A dermoscopic photograph of a skin lesion.
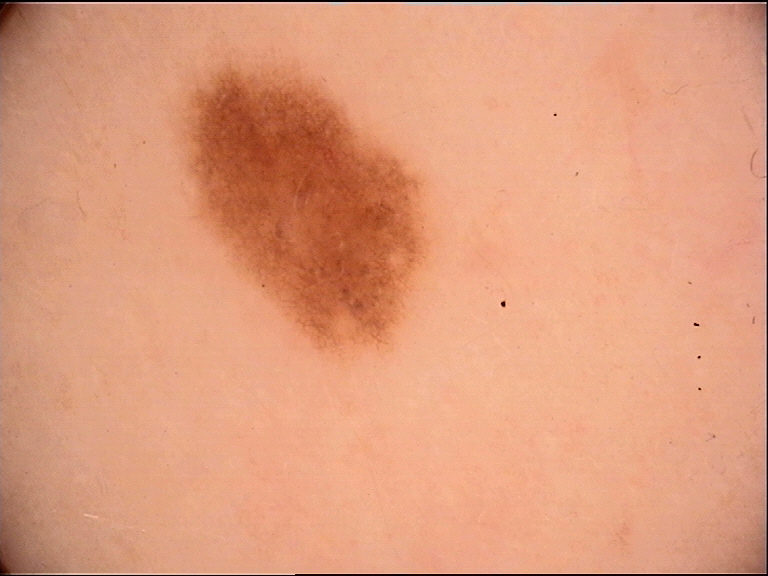The diagnosis was a dysplastic junctional nevus.